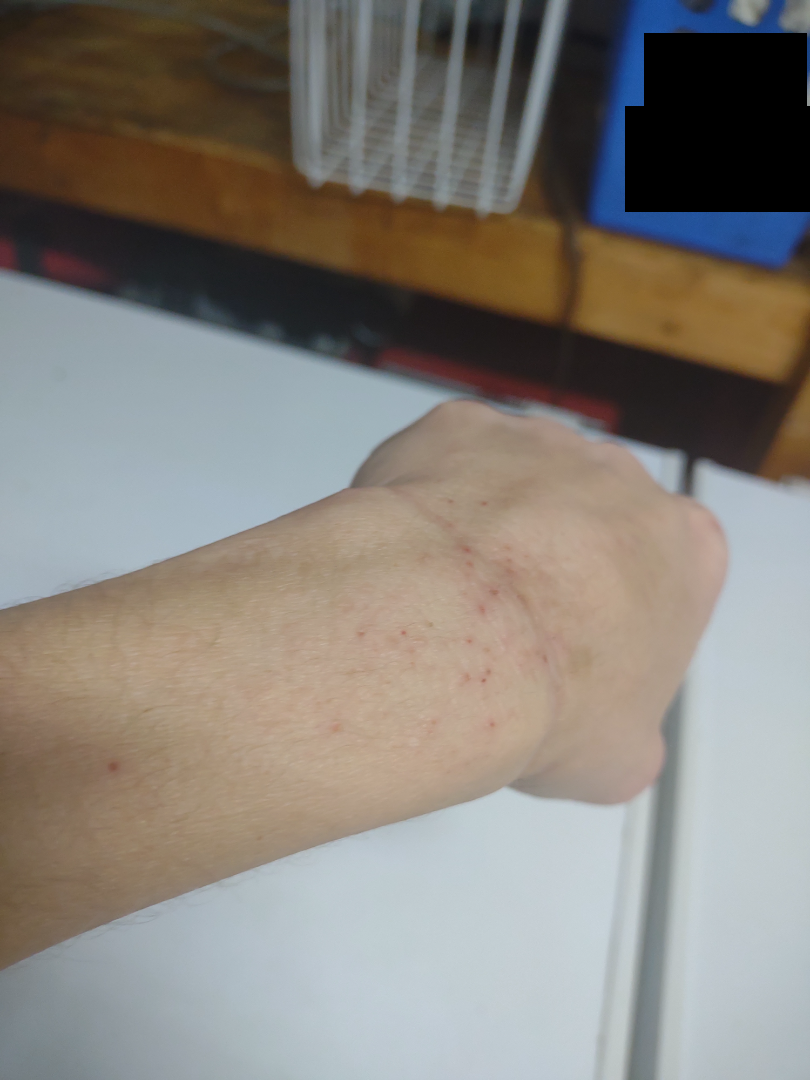The skin condition could not be confidently assessed from this image. The contributor notes the condition has been present for less than one week. An image taken at a distance. The contributor is a female aged 30–39. No associated systemic symptoms reported. The patient described the issue as a rash. The contributor notes the lesion is raised or bumpy. The lesion is associated with itching.